A dermoscopic photograph of a skin lesion: 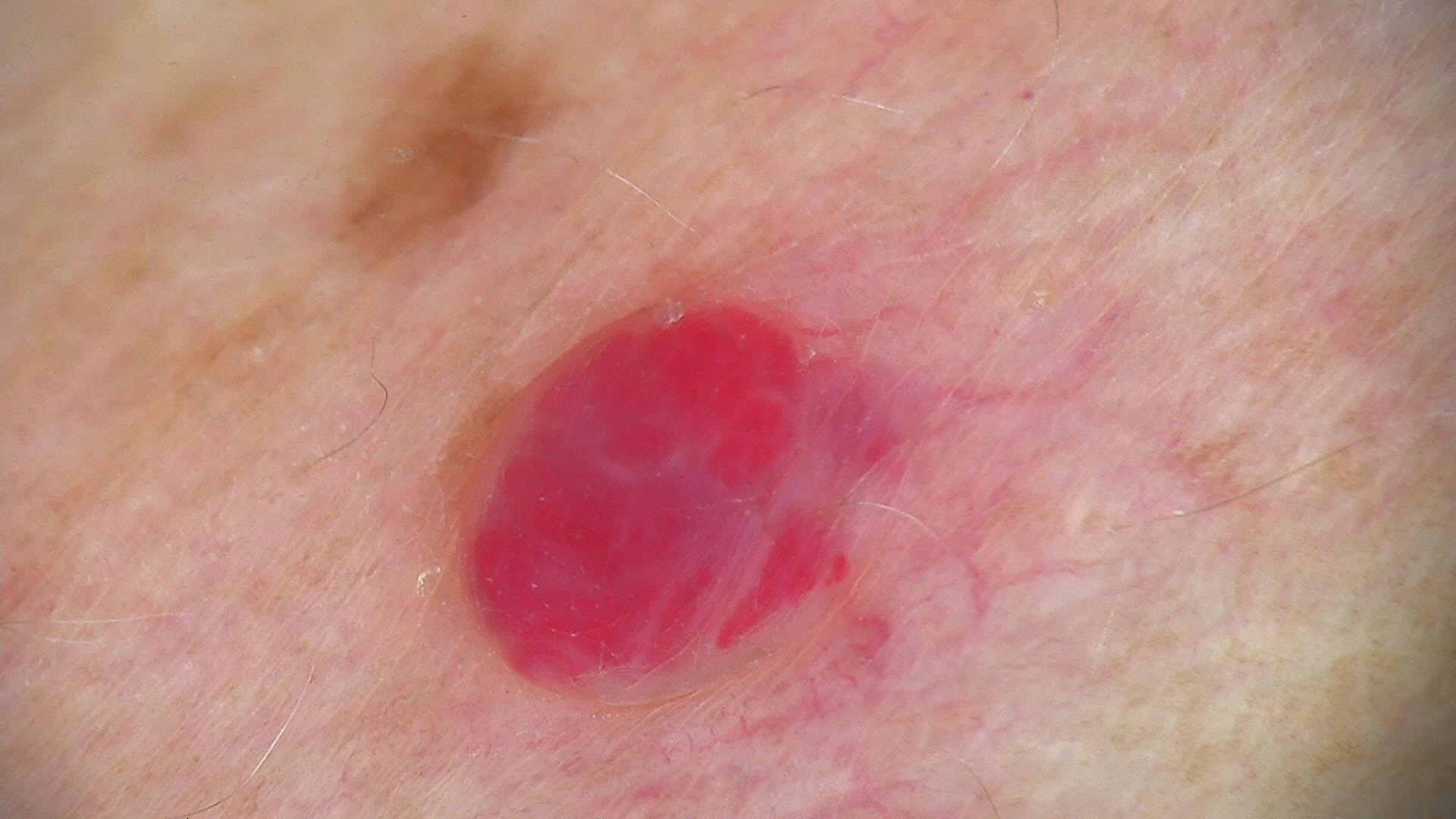| feature | finding |
|---|---|
| label | hemangioma (expert consensus) |